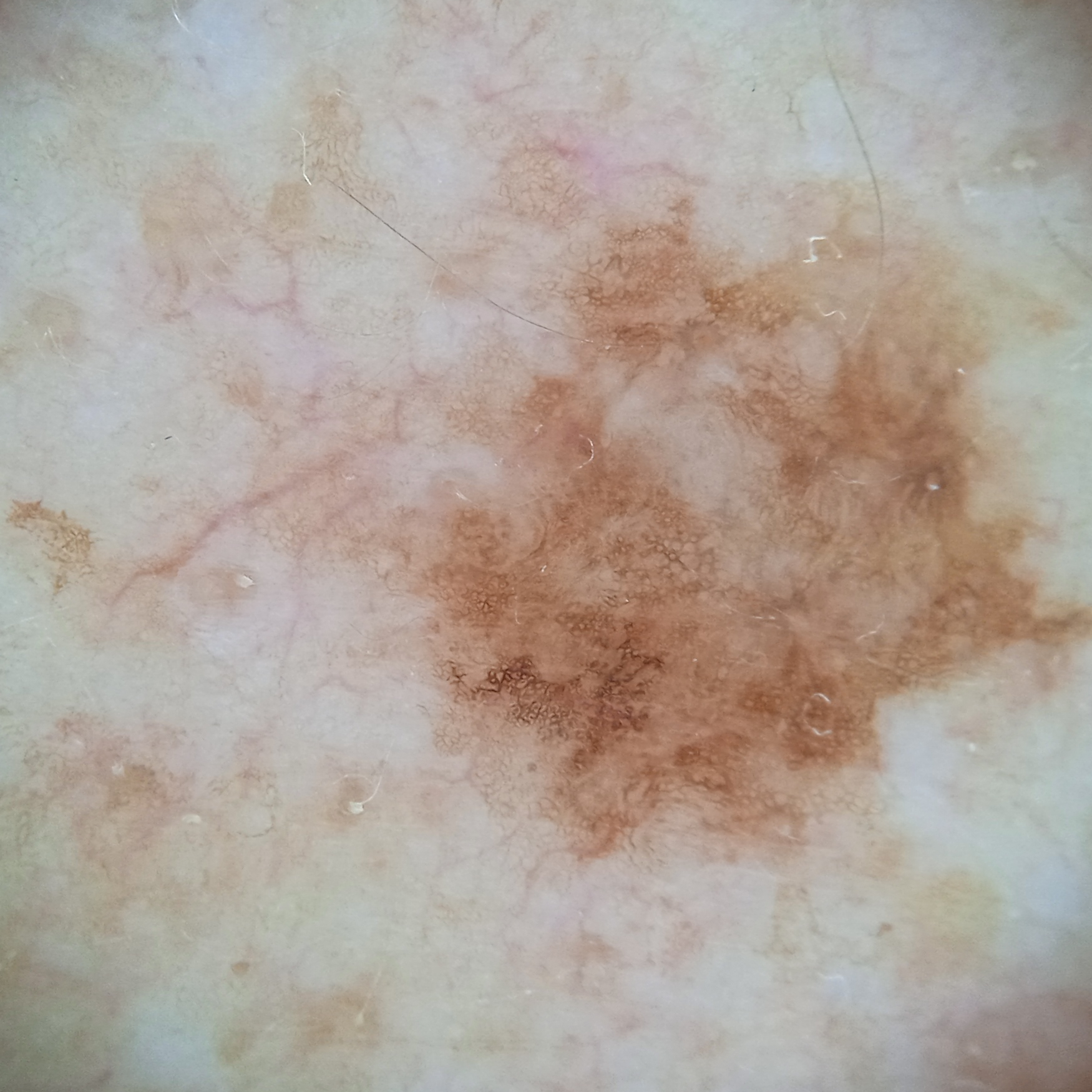The lesion was left diagnostically undetermined on review.